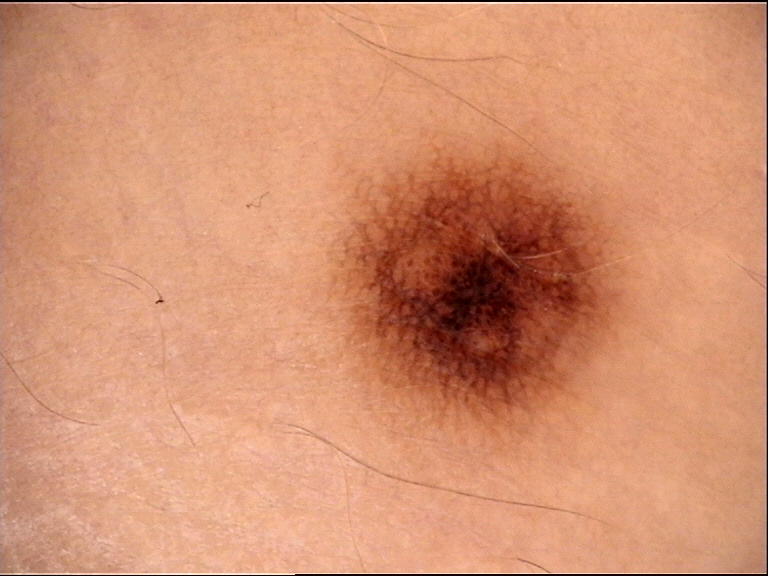diagnosis:
  name: dysplastic junctional nevus
  code: jd
  malignancy: benign
  super_class: melanocytic
  confirmation: expert consensus